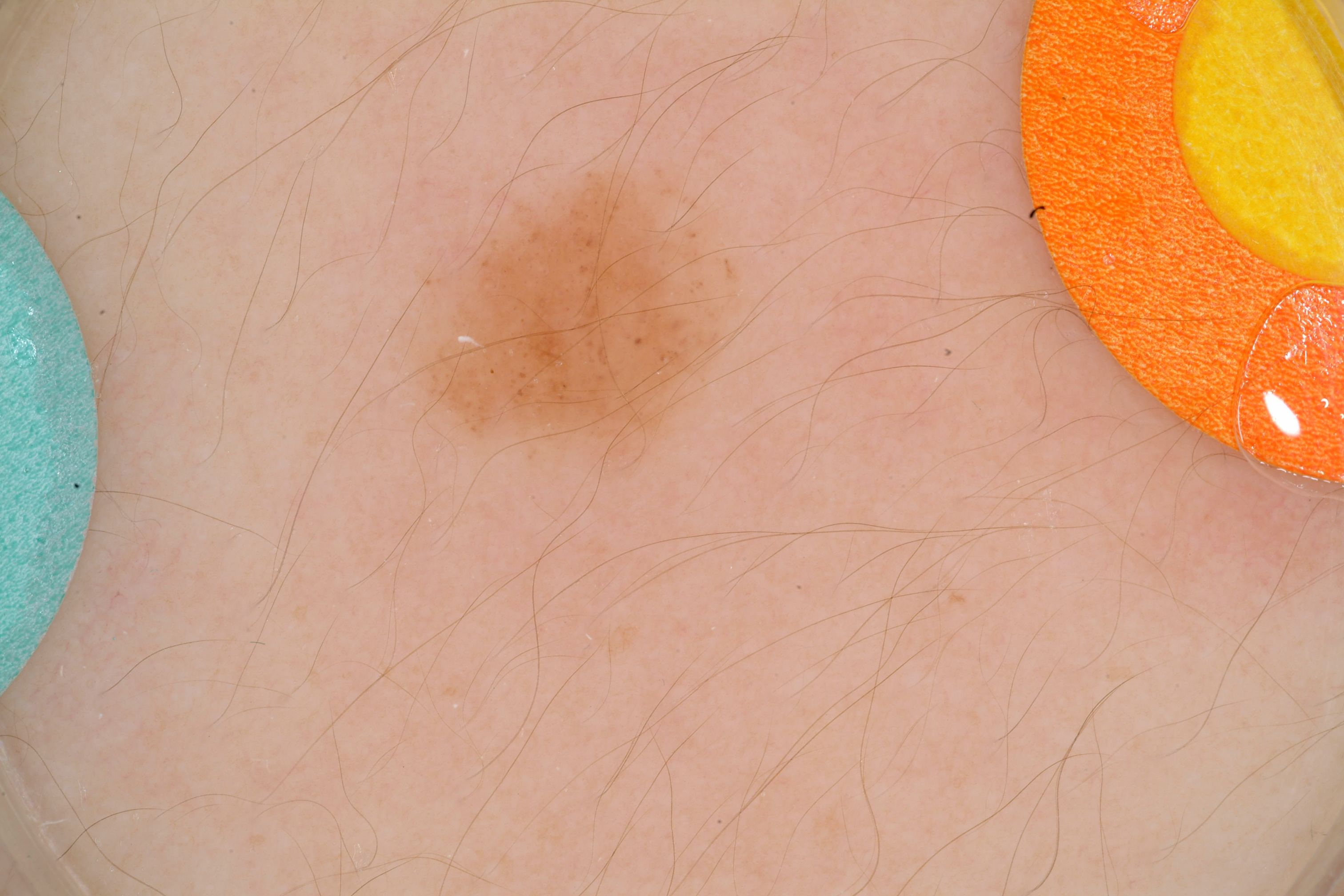Q: What kind of image is this?
A: dermatoscopic image of a skin lesion
Q: Where is the lesion in the image?
A: [405, 161, 750, 499]
Q: Which dermoscopic features are absent?
A: globules and streaks
Q: How much of the field does the lesion occupy?
A: ~6% of the field
Q: What did the assessment conclude?
A: a benign lesion